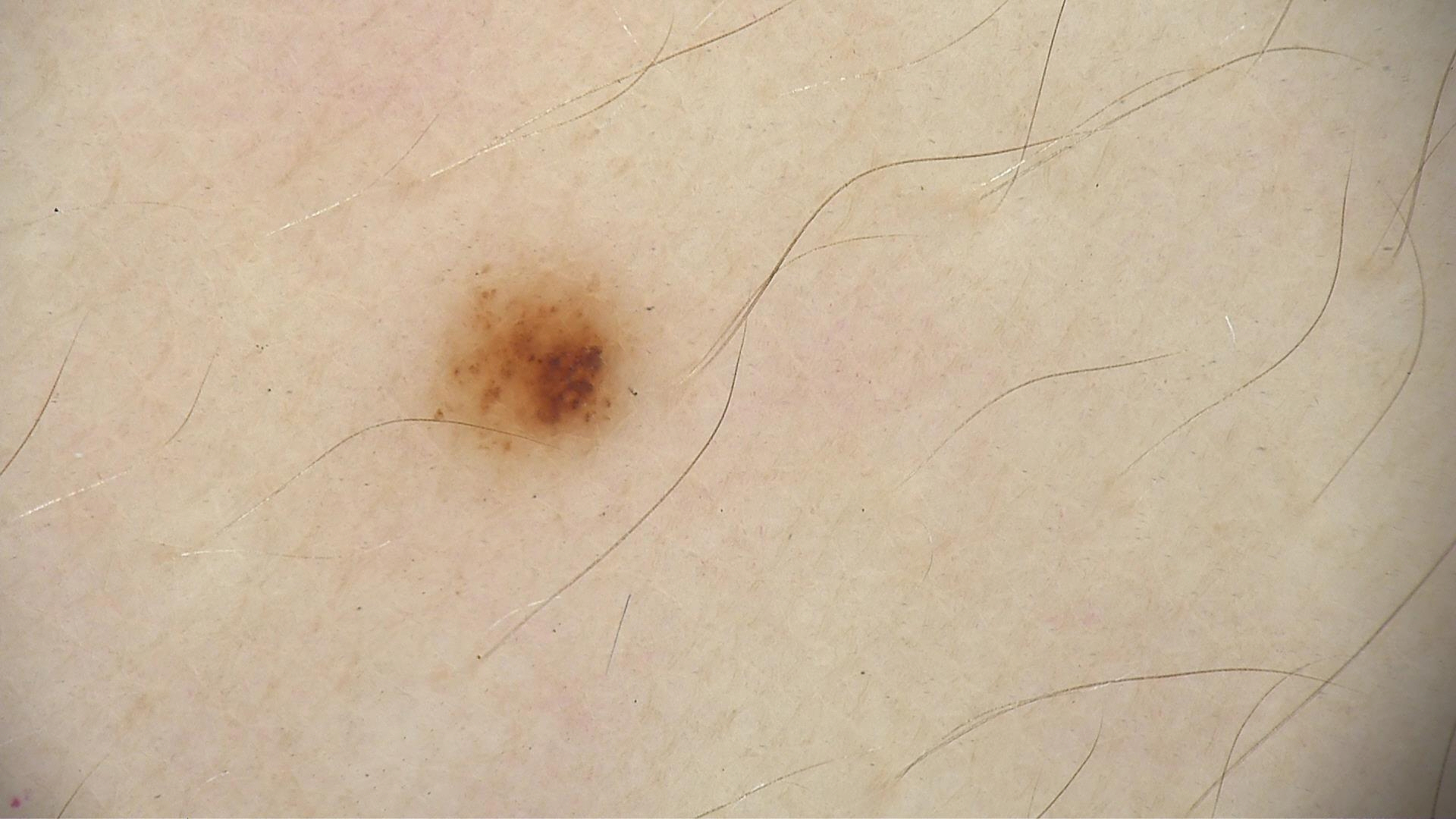A dermoscopic close-up of a skin lesion. The diagnosis was a benign lesion — a dysplastic junctional nevus.